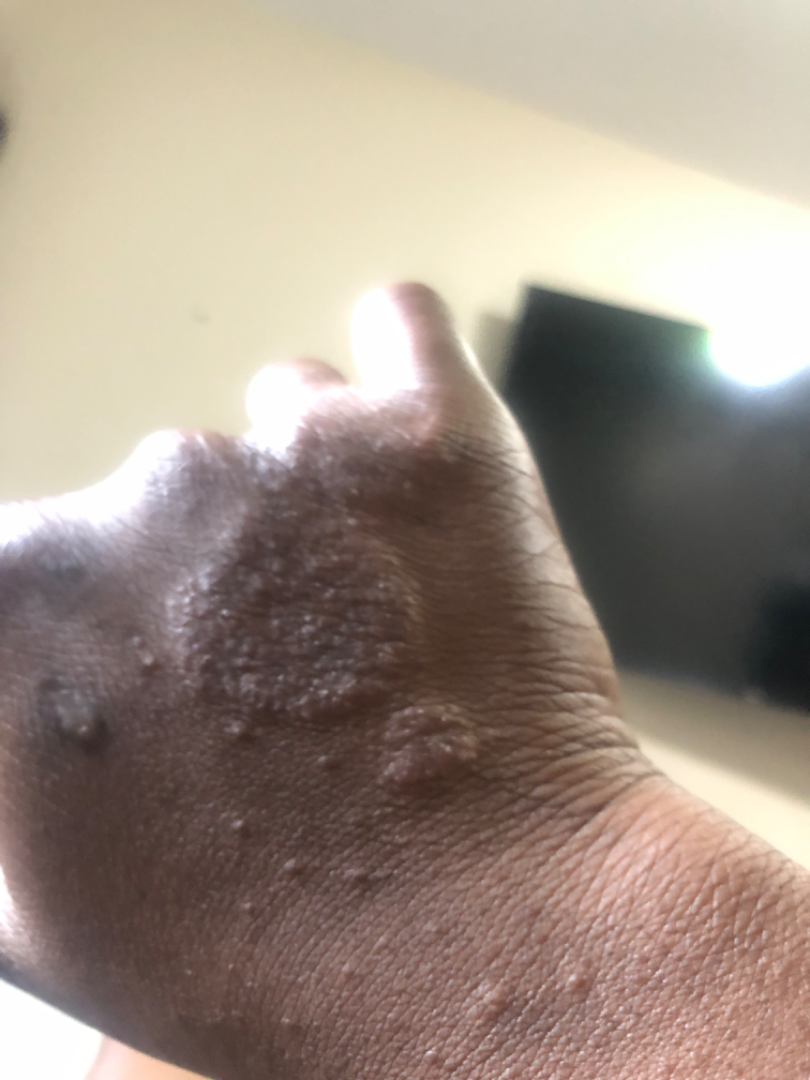Close-up view. Single-reviewer assessment: most consistent with Chronic dermatitis, NOS.